The affected area is the leg, this image was taken at an angle, symptoms reported: itching, no associated systemic symptoms reported, the patient described the issue as a rash:
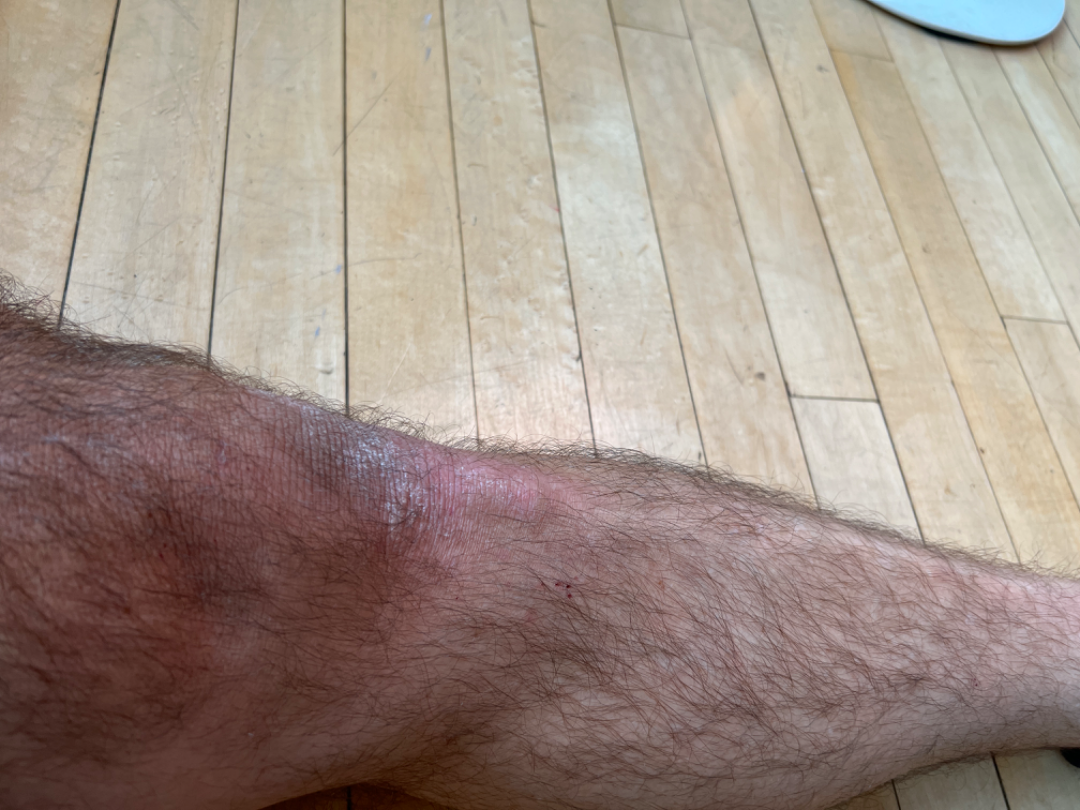Most consistent with Psoriasis.